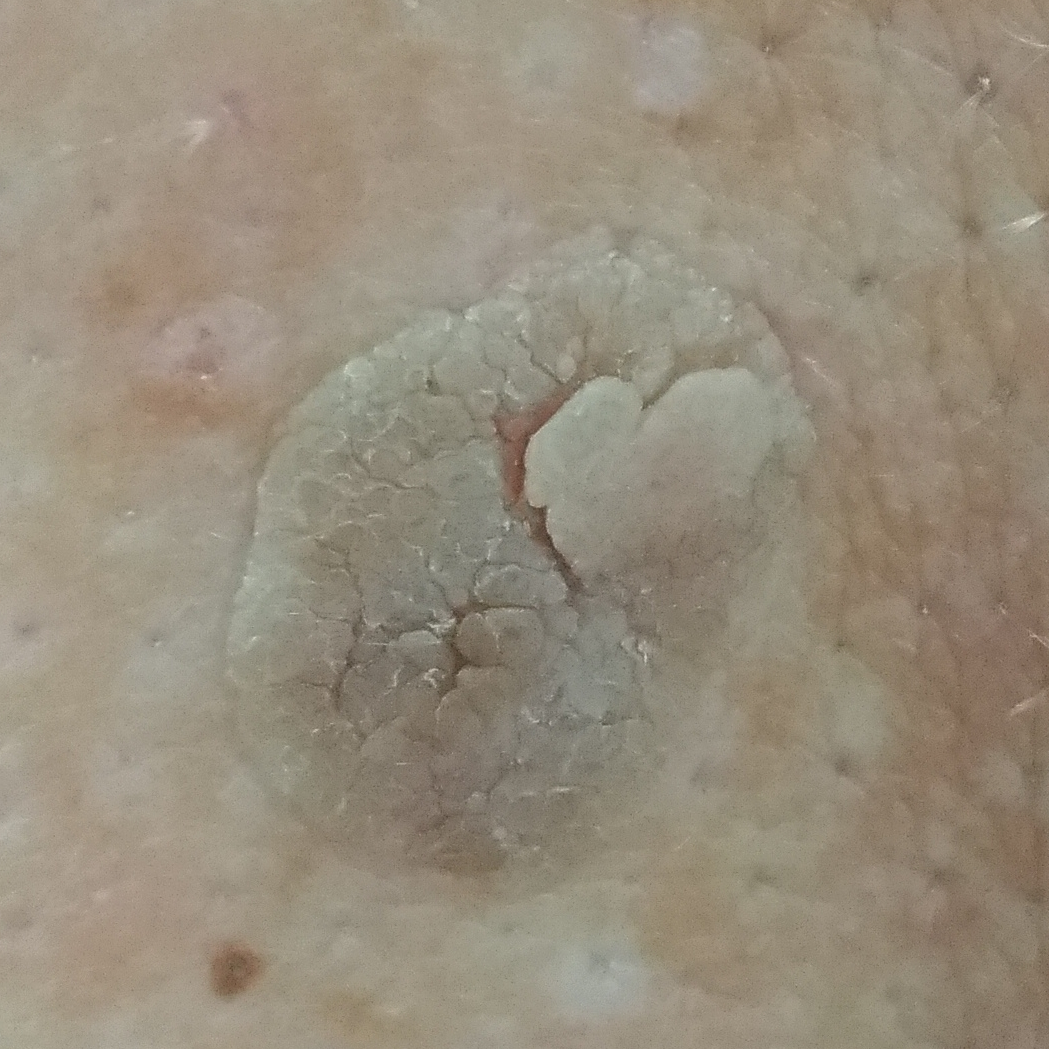A smartphone photograph of a skin lesion.
A subject age 62.
The lesion is on the back.
The patient reports that the lesion has grown, itches, and is elevated.
Clinically diagnosed as a benign lesion — a seborrheic keratosis.